A macroscopic clinical photograph of a skin lesion. A male subject 83 years old. The patient says their skin reddens with sun exposure: 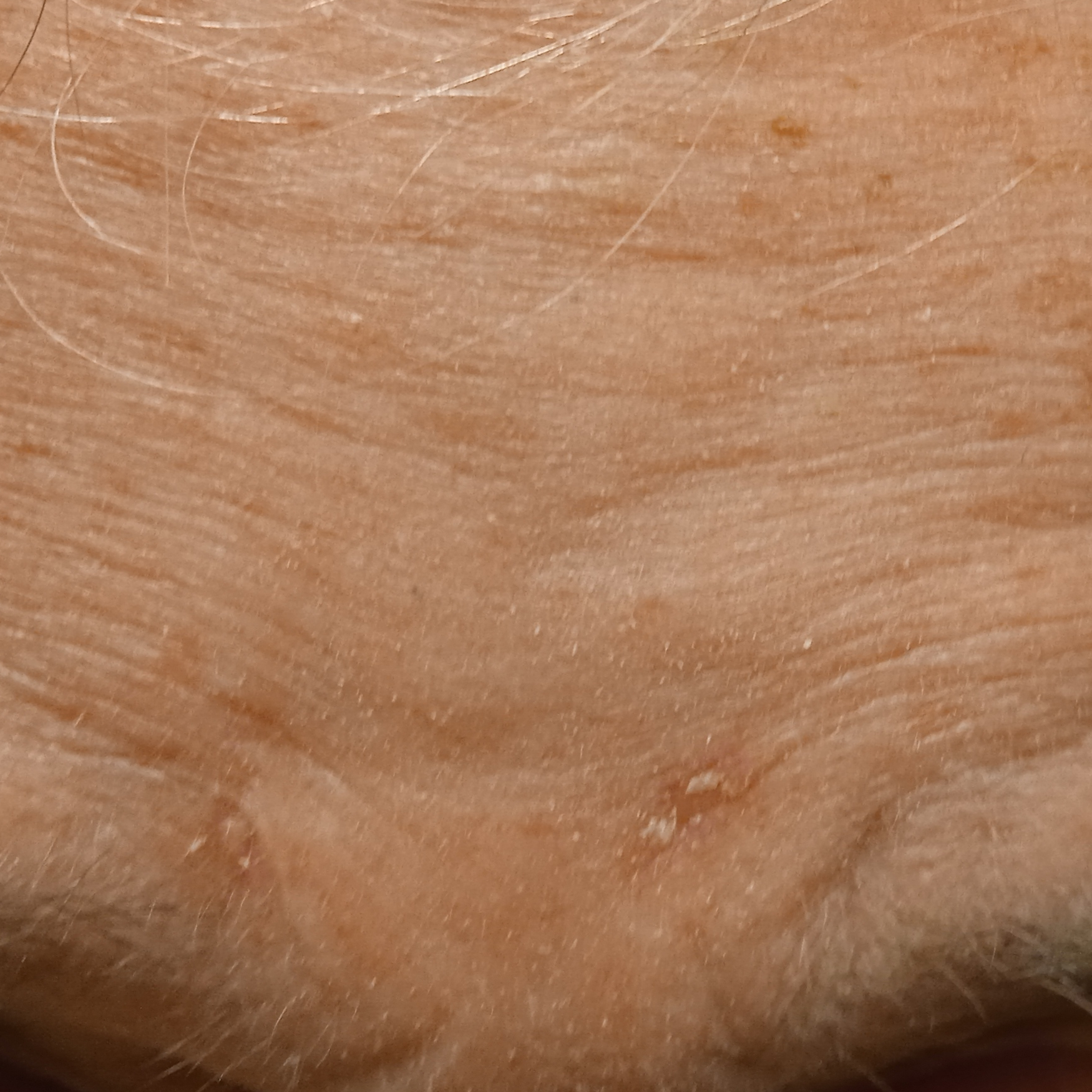location: the face; lesion size: 7.5 mm; diagnosis: actinic keratosis (dermatologist consensus).